The photo was captured at a distance · female patient, age 18–29:
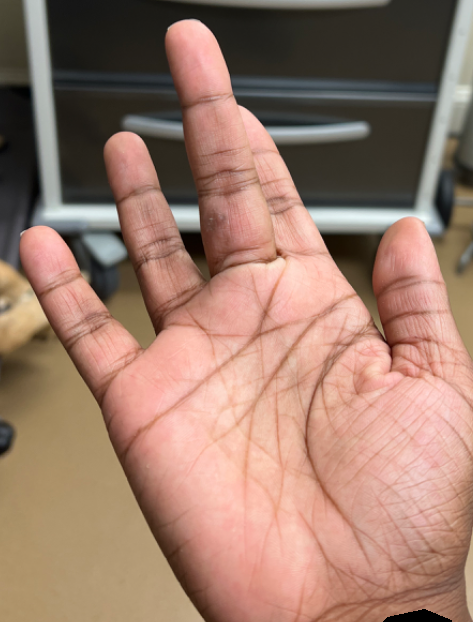Case summary:
- assessment — reviewed remotely by three dermatologists: the favored diagnosis is Verruca vulgaris; less likely is Clavus; lower on the differential is Psoriasis; a more distant consideration is Allergic Contact Dermatitis; less probable is Eczema